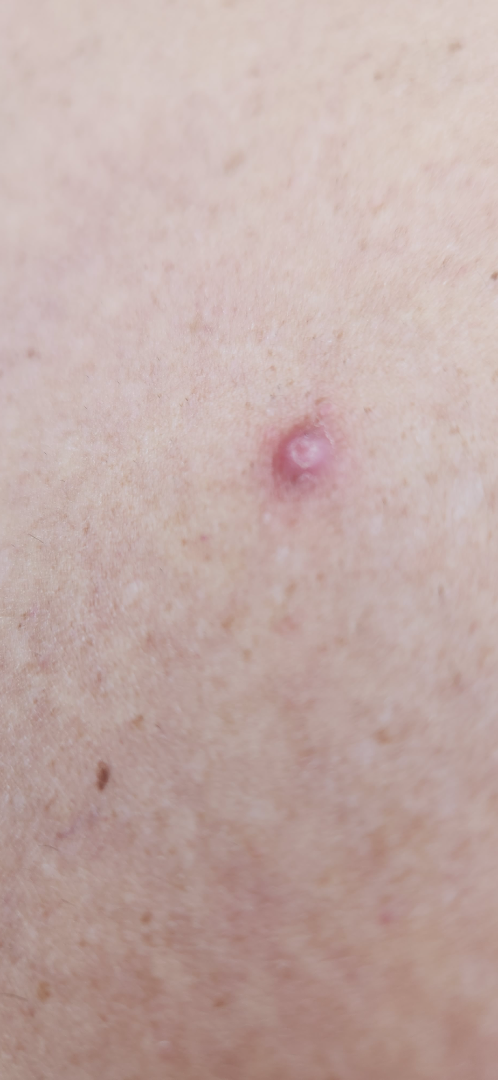Case summary:
• clinical impression: favoring Molluscum Contagiosum; an alternative is Folliculitis; lower on the differential is SCC/SCCIS